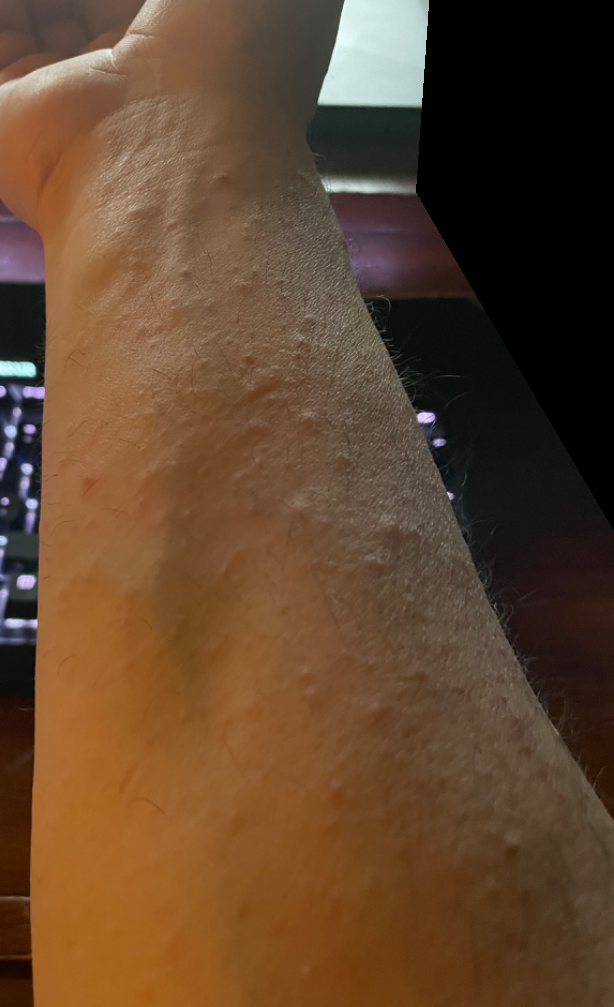On remote review of the image, the favored diagnosis is Eczema; an alternative is Scabies.